A dermoscopic close-up of a skin lesion: 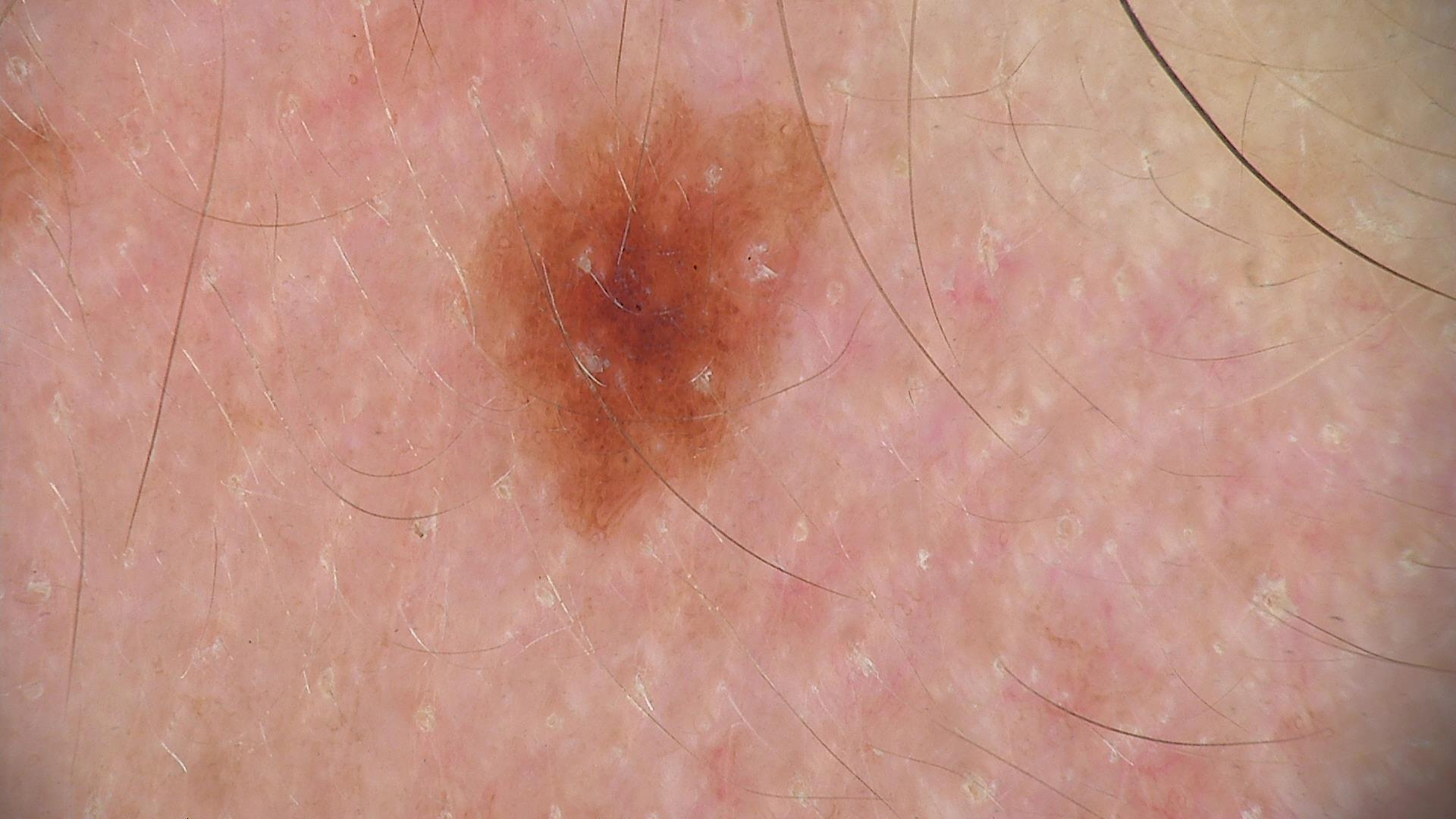Impression:
The diagnosis was a benign lesion — a dysplastic junctional nevus.